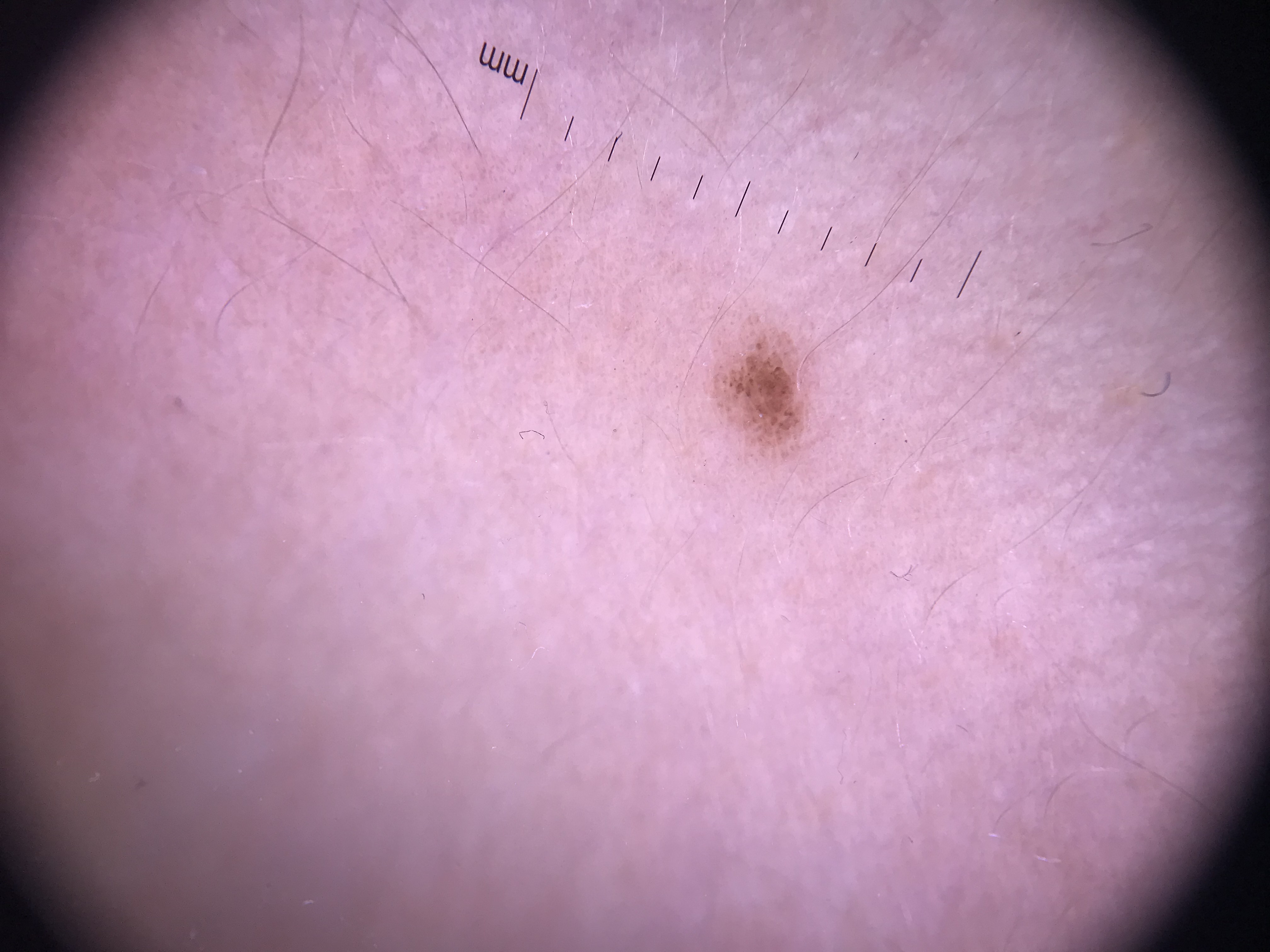Summary: A skin lesion imaged with a dermatoscope. This is a banal lesion. Conclusion: Labeled as a junctional nevus.